A dermoscopic photograph of a skin lesion.
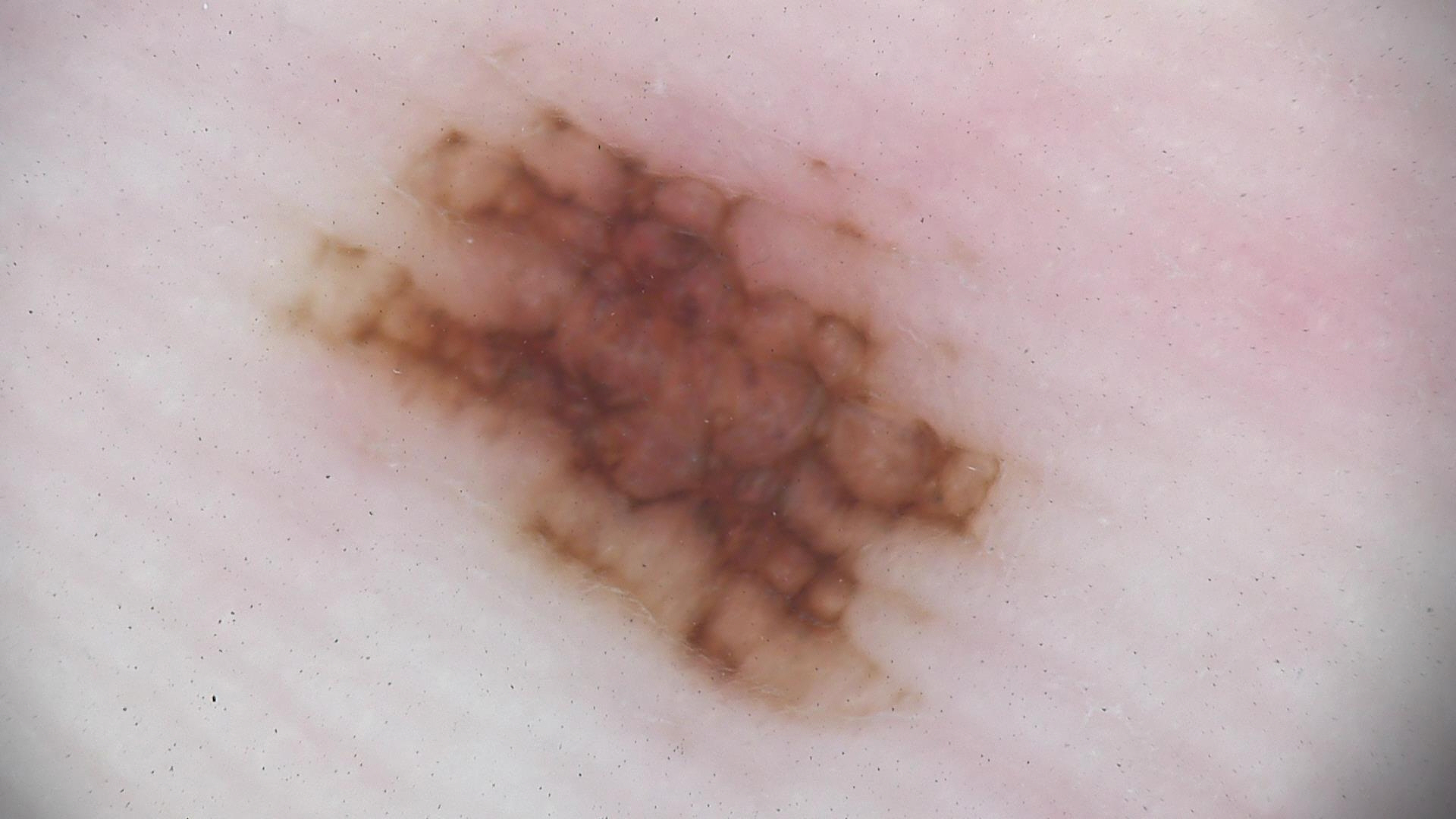{"diagnosis": {"name": "acral dysplastic junctional nevus", "code": "ajd", "malignancy": "benign", "super_class": "melanocytic", "confirmation": "expert consensus"}}